Male subject, age 30–39; the lesion involves the front of the torso and back of the torso; an image taken at a distance:
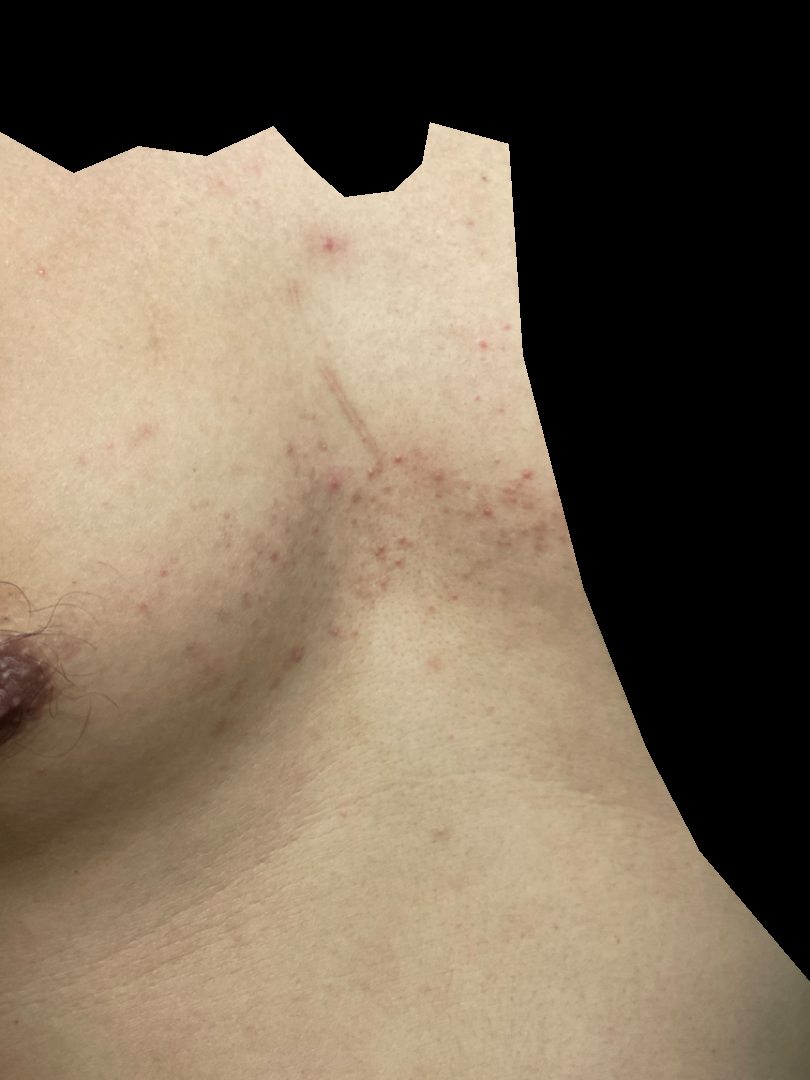self-categorized as = a rash
lesion texture = raised or bumpy
differential = the primary impression is Folliculitis